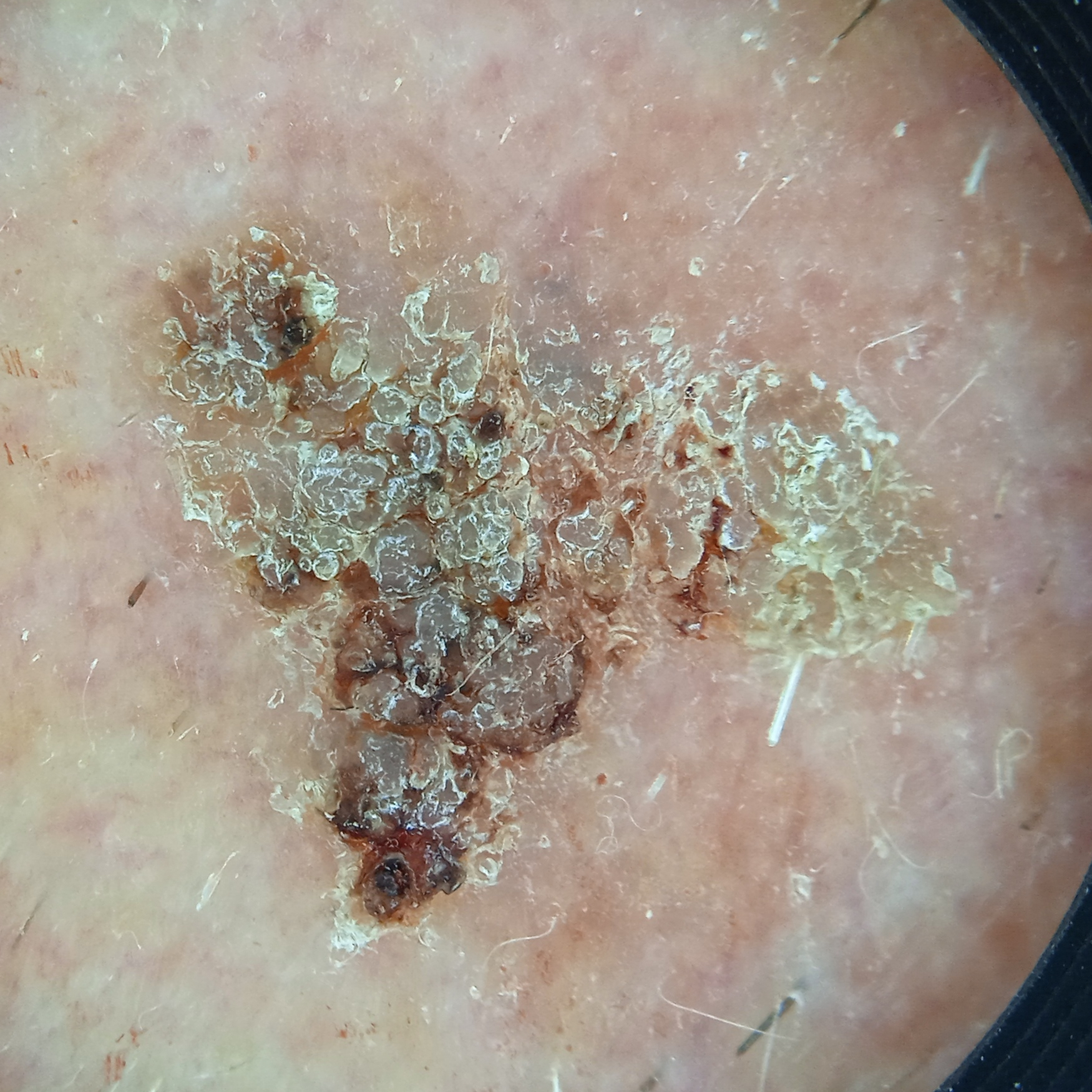<lesion>
<referral>research study (no referral diagnosis)</referral>
<risk_factors>
<positive>a personal history of cancer</positive>
</risk_factors>
<lesion_location>the face</lesion_location>
<diagnosis>
<name>seborrheic keratosis</name>
<malignancy>benign</malignancy>
</diagnosis>
</lesion>